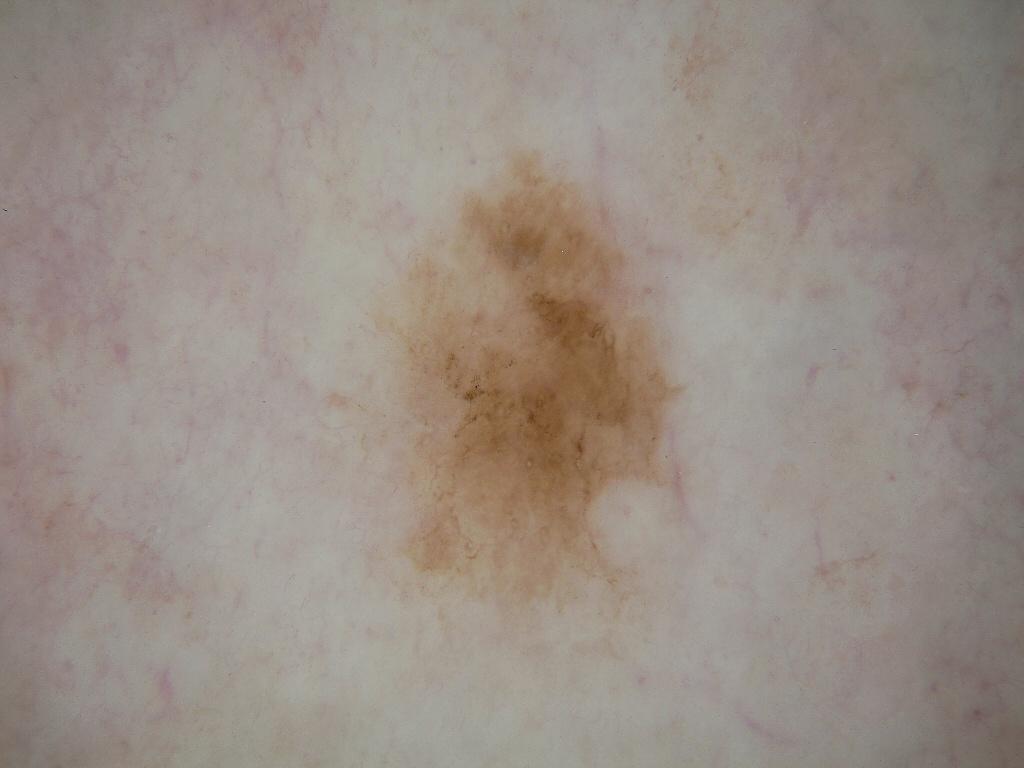image type: dermoscopic image | subject: female, approximately 55 years of age | dermoscopic findings: pigment network | lesion size: moderate | bounding box: <bbox>370, 148, 687, 636</bbox> | diagnosis: a melanoma, a skin cancer.